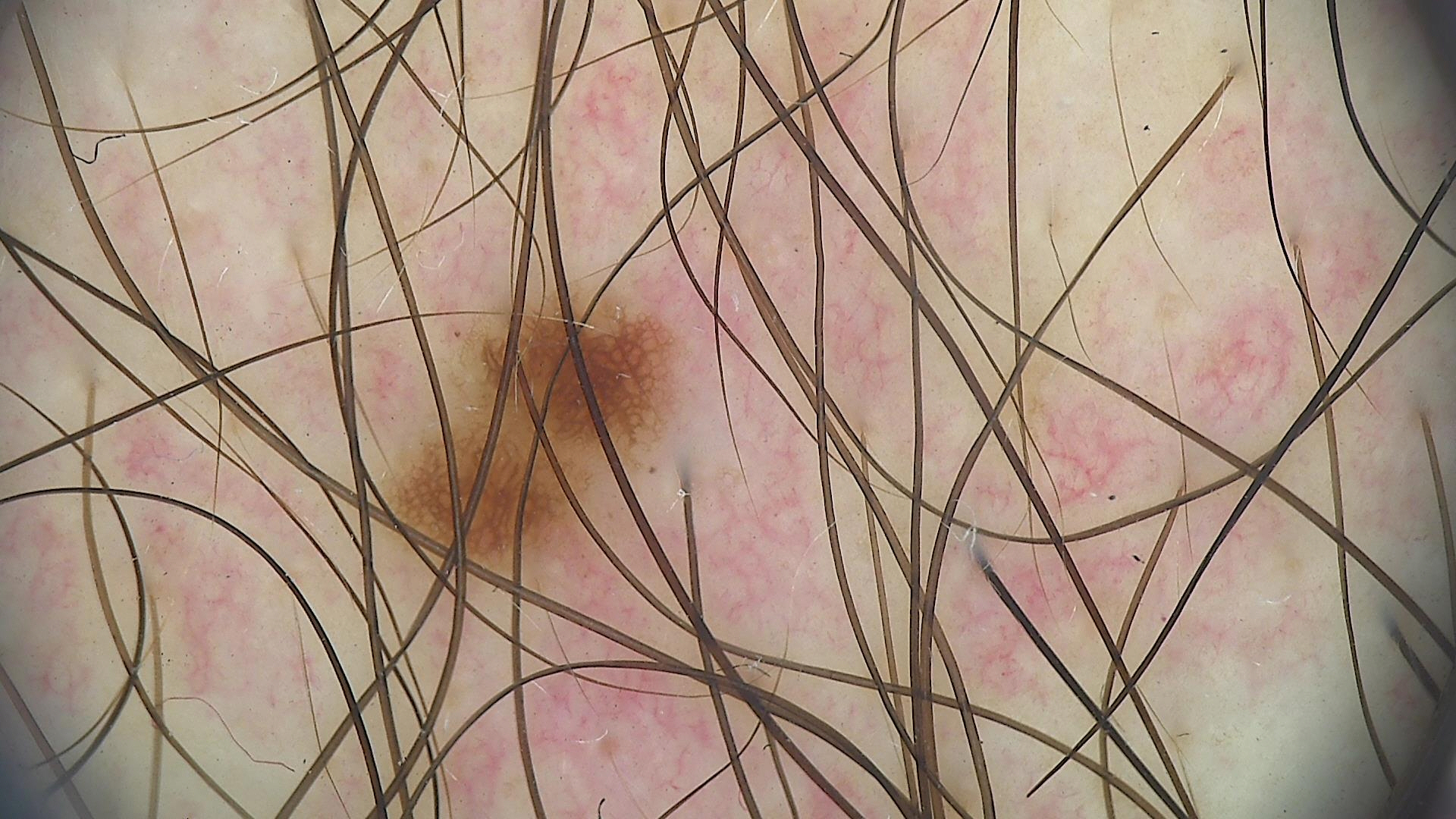Case: A dermoscopic photograph of a skin lesion. Conclusion: Consistent with a benign lesion — a dysplastic junctional nevus.